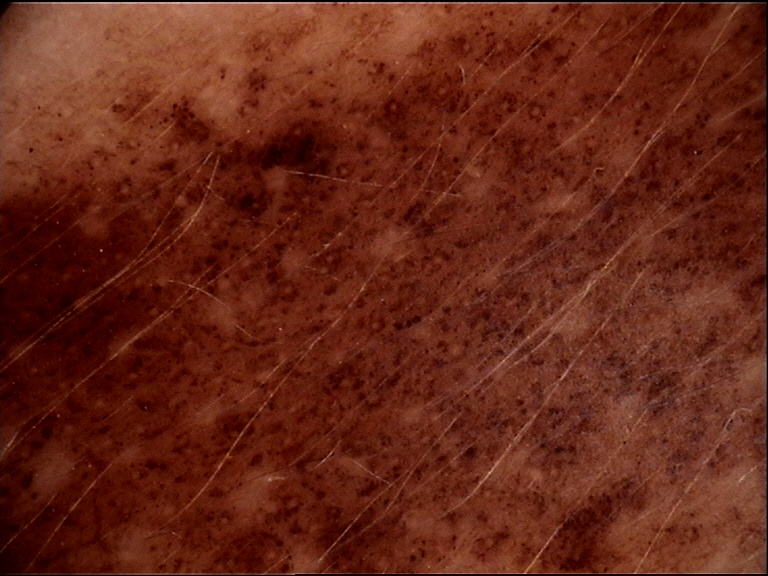Case:
* modality · dermatoscopy
* diagnostic label · congenital compound nevus (expert consensus)